A female subject approximately 60 years of age; dermoscopy of a skin lesion:
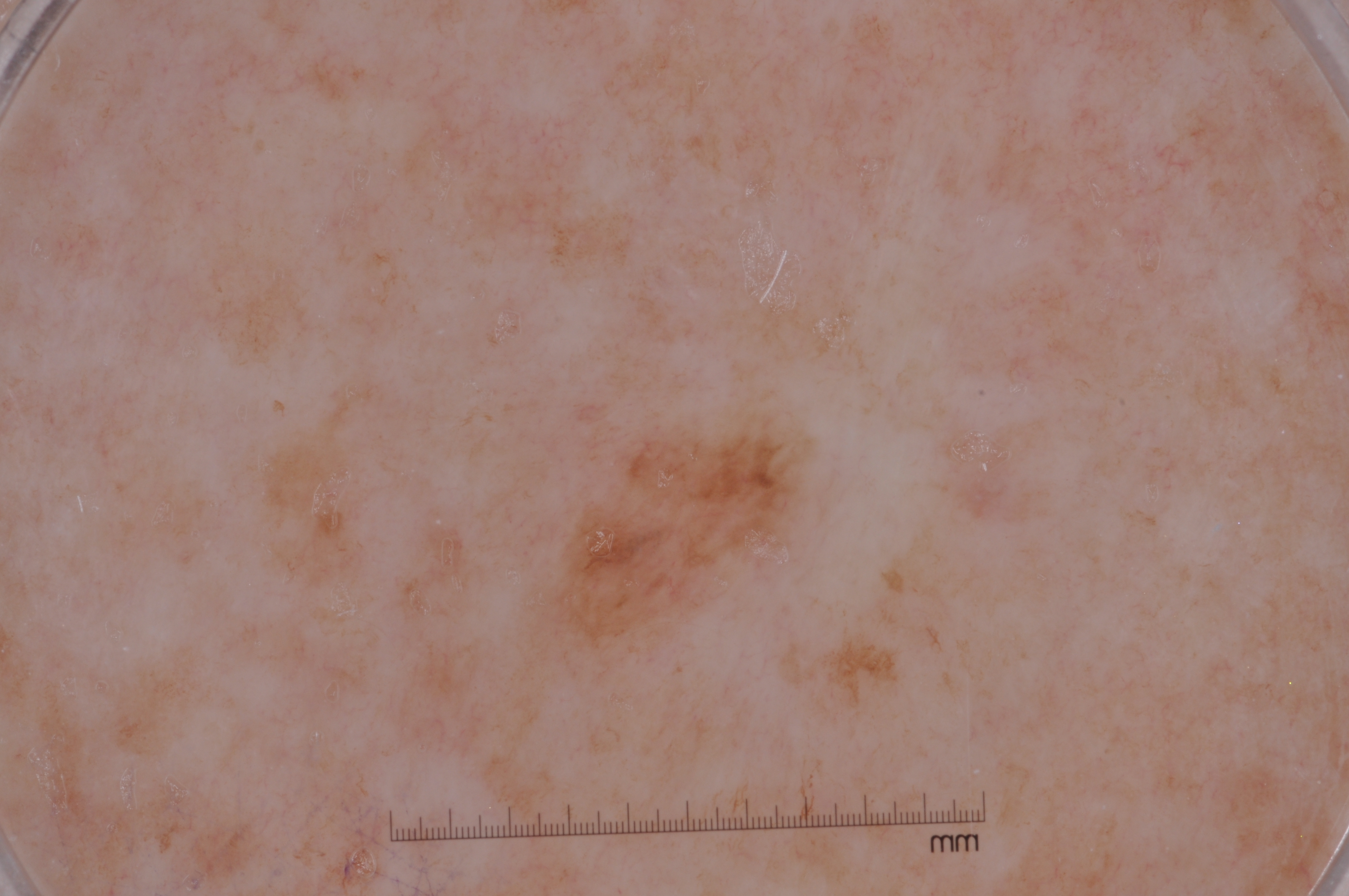Dermoscopic examination shows no negative network, pigment network, streaks, or milia-like cysts. The lesion is bounded by left=559, top=421, right=801, bottom=637. The lesion occupies roughly 3% of the field. The biopsy diagnosis was a melanoma.